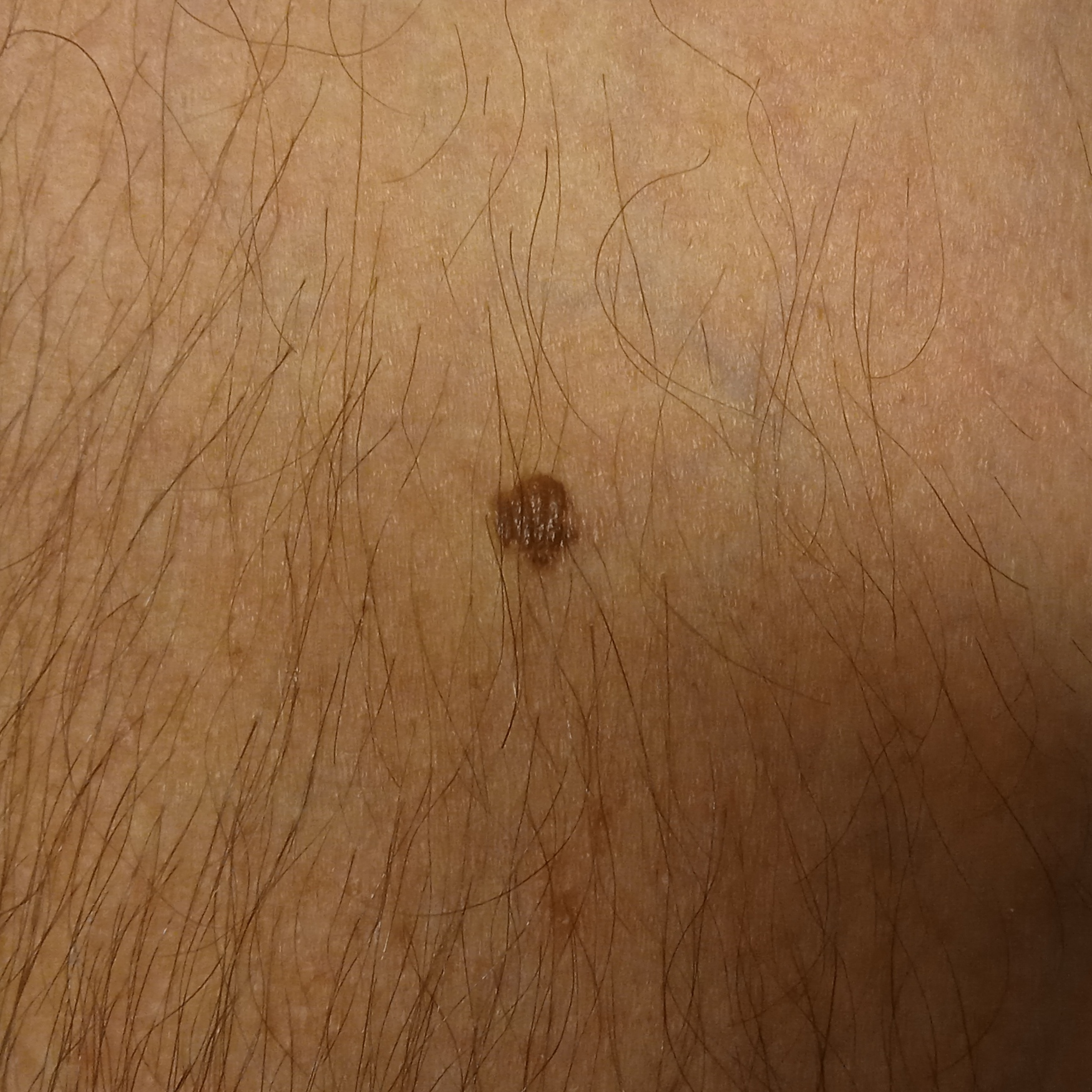Collected as part of a research study, without a referral diagnosis. A macroscopic clinical photograph of a skin lesion. A male subject aged 65. The patient reports a personal history of skin cancer, immunosuppression, and a family history of skin cancer. The patient says their skin reddens painfully with sun exposure. The lesion is located on an arm. The dermatologists' assessment was a melanocytic nevus.